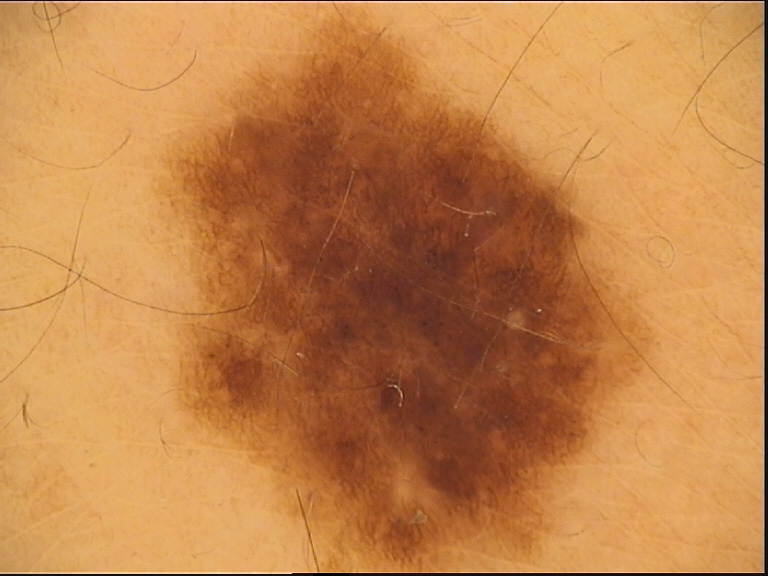A dermoscopic close-up of a skin lesion.
Consistent with a benign lesion — a dysplastic compound nevus.